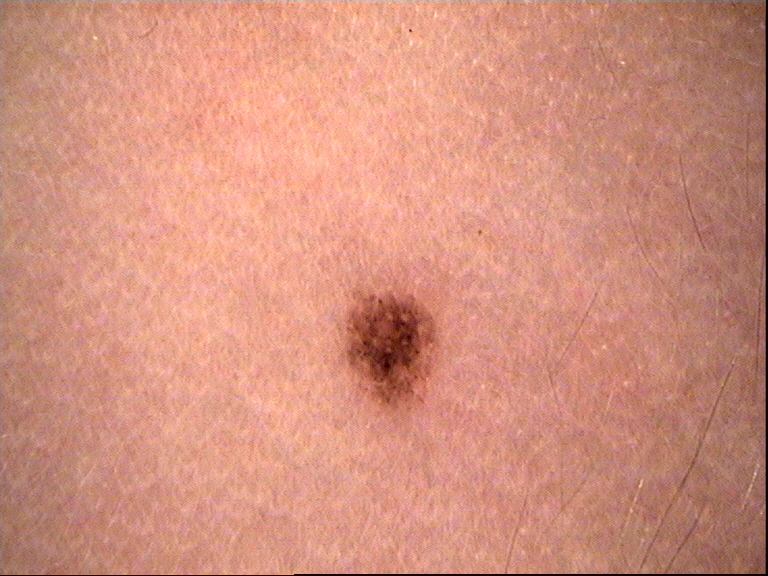Findings:
- imaging: dermoscopy
- assessment: dysplastic junctional nevus (expert consensus)